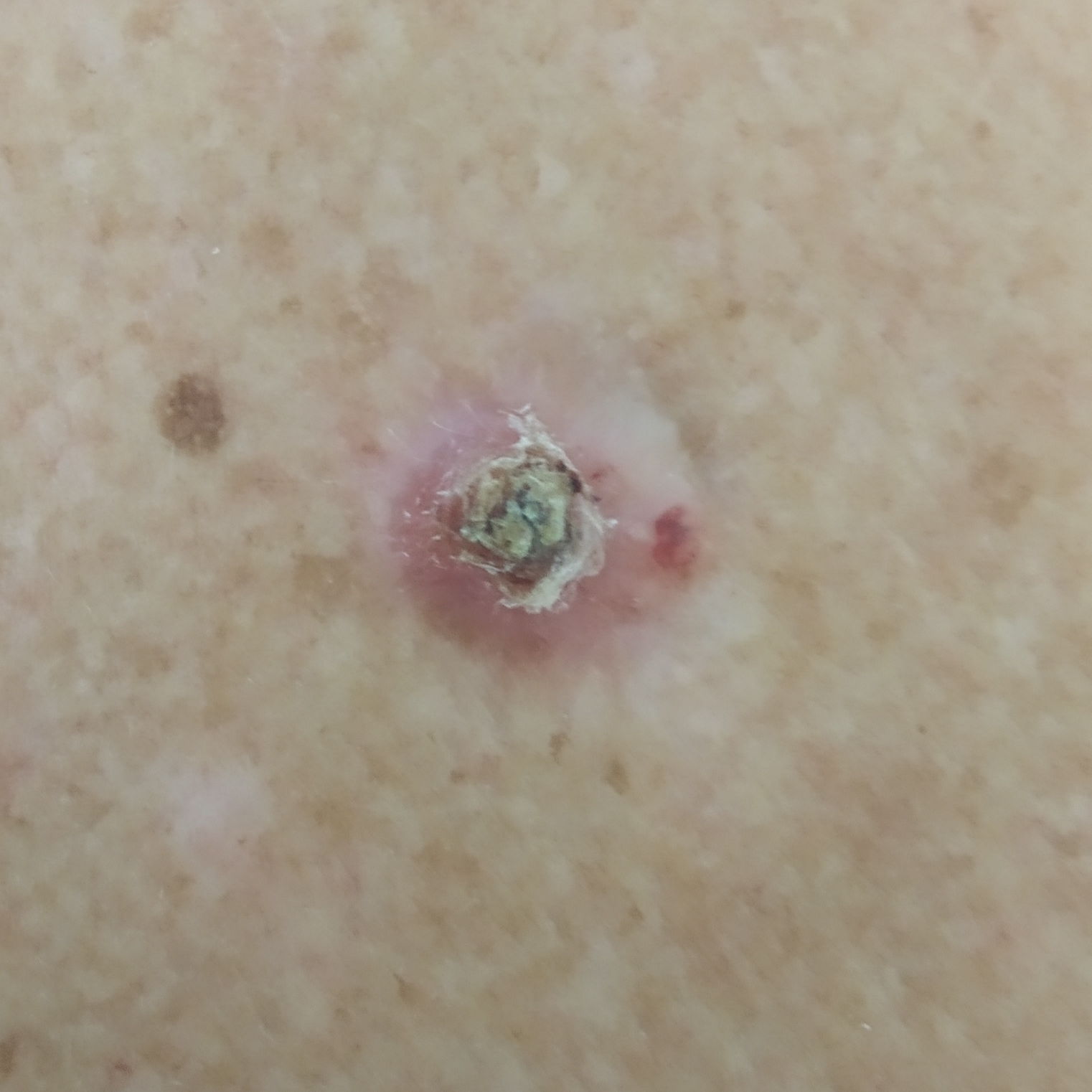Findings:
- skin phototype: II
- subject: male, age 65
- site: the back
- lesion size: approx. 16 × 15 mm
- patient-reported symptoms: itching, elevation, bleeding / no pain
- diagnostic label: basal cell carcinoma (biopsy-proven)